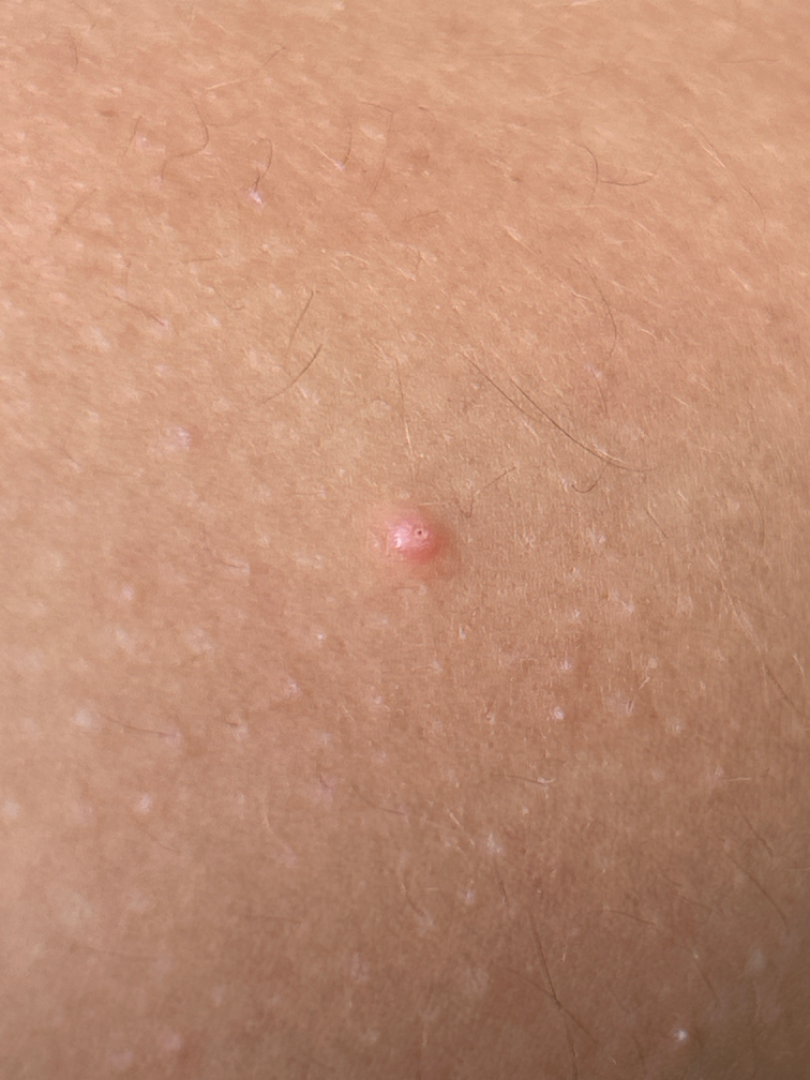Notes:
* differential — a single dermatologist reviewed the case: in keeping with Molluscum Contagiosum